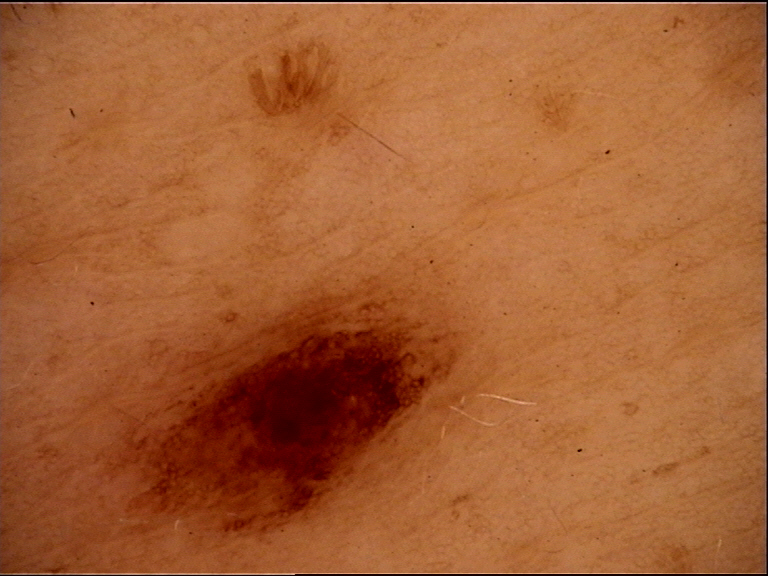class = dysplastic compound nevus (expert consensus).